The patient is a female aged 18–29 · the leg is involved · reported lesion symptoms include itching, enlargement, bothersome appearance, burning and pain · the photograph is a close-up of the affected area · no relevant systemic symptoms · self-categorized by the patient as a rash — 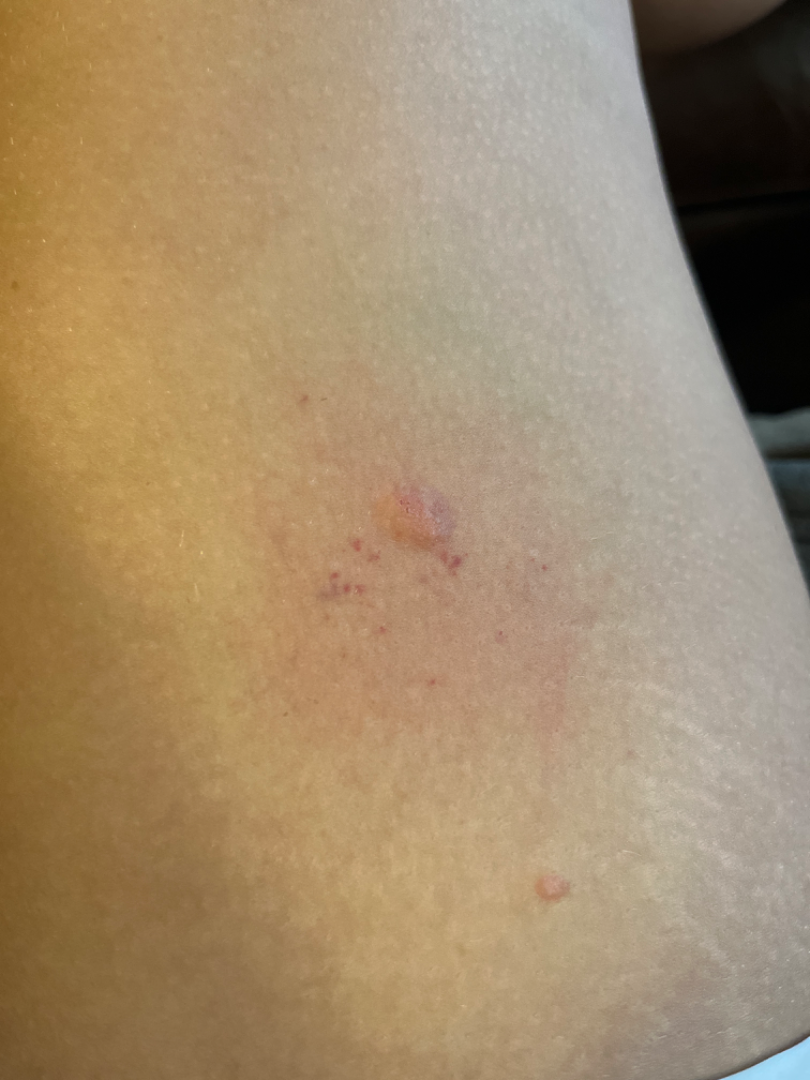Findings: The reviewing clinician's impression was: Verruca vulgaris and SCC/SCCIS were considered with similar weight.